A patient age 50 · a clinical close-up photograph of a skin lesion: 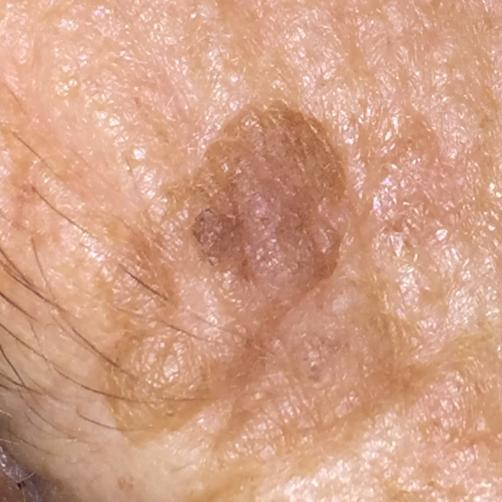Located on the face. Per patient report, the lesion has grown. The diagnostic impression was a benign lesion — a seborrheic keratosis.